The contributor notes the condition has been present for more than five years · the photograph was taken at a distance · the lesion involves the back of the hand and palm · the subject is 18–29, male · the lesion is described as raised or bumpy · the contributor notes pain and itching — 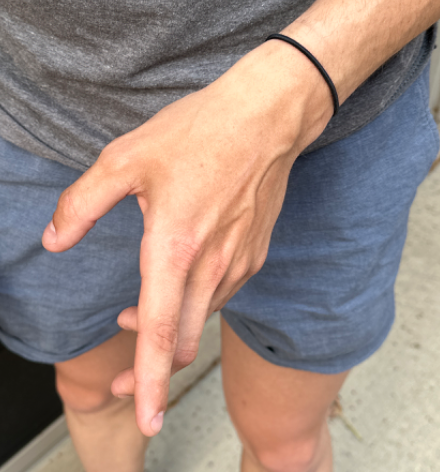The skin findings could not be characterized from the image.